The patient reports a family history of skin cancer, a personal history of cancer, and a personal history of skin cancer; a dermatoscopic image of a skin lesion; imaged for a research study, with no referral diagnosis recorded; a female patient 58 years old; the patient says their skin tans without first burning: 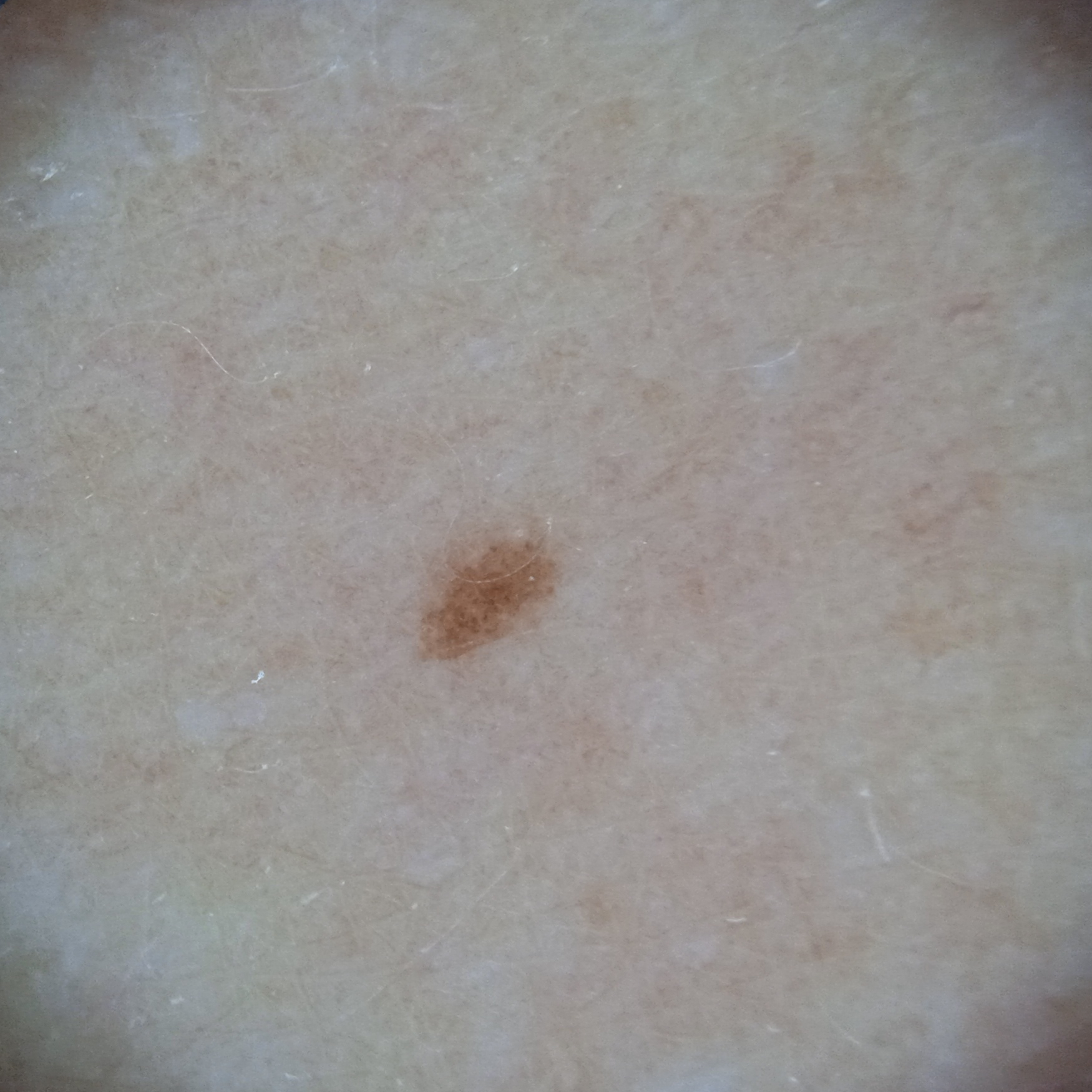diameter = 1.9 mm; diagnosis = melanocytic nevus (dermatologist consensus).